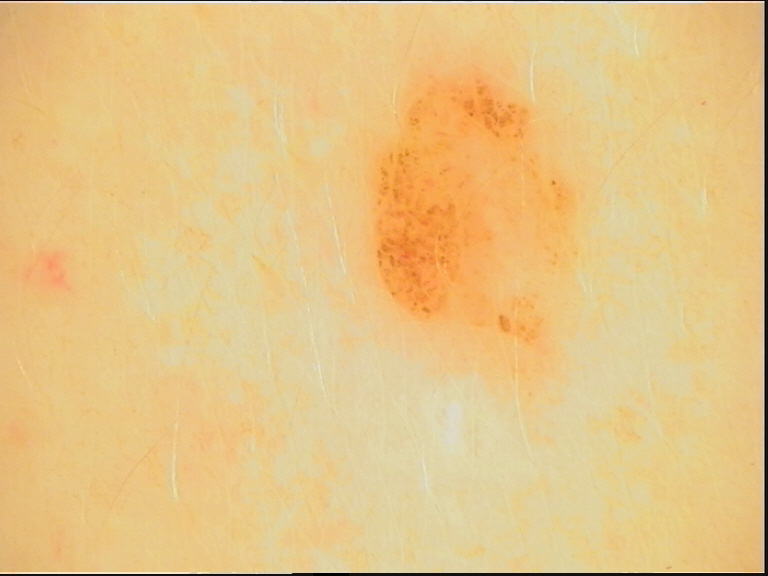A dermoscopic image of a skin lesion.
Labeled as a banal lesion — a compound nevus.